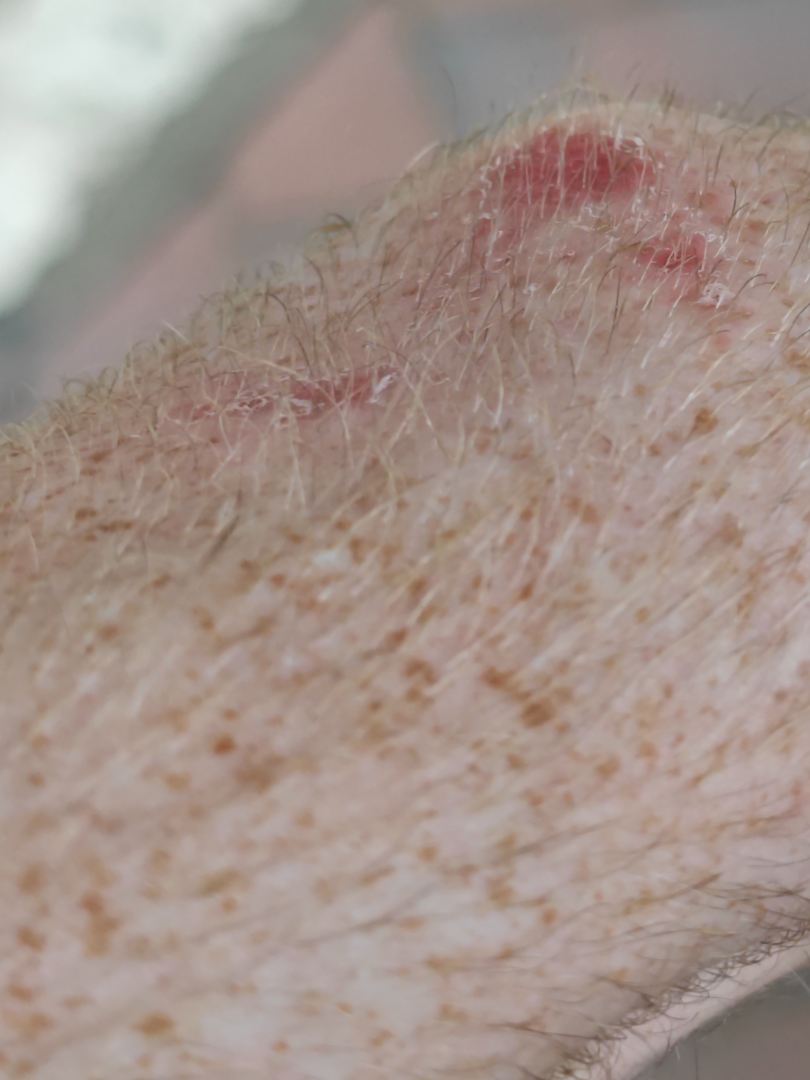The contributor notes the lesion is rough or flaky.
Reported duration is one to four weeks.
The photo was captured at an angle.
The patient described the issue as a rash.
The arm is involved.
Symptoms reported: itching and bothersome appearance.
The patient is 18–29, male.
Favoring Superficial wound of body region; with consideration of SCC/SCCIS.